The affected area is the arm, back of the hand and leg · an image taken at a distance — 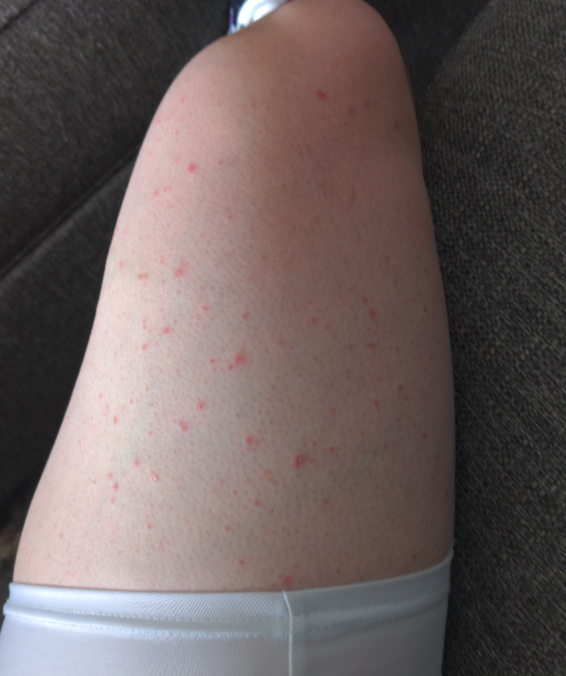Folliculitis (most likely); Porokeratosis (considered).